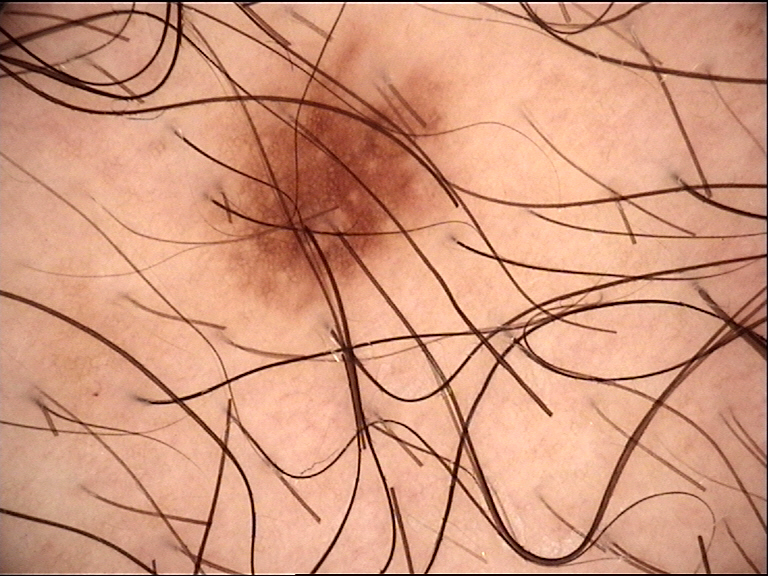- diagnostic label: dysplastic junctional nevus (expert consensus)